Dermoscopy of a skin lesion.
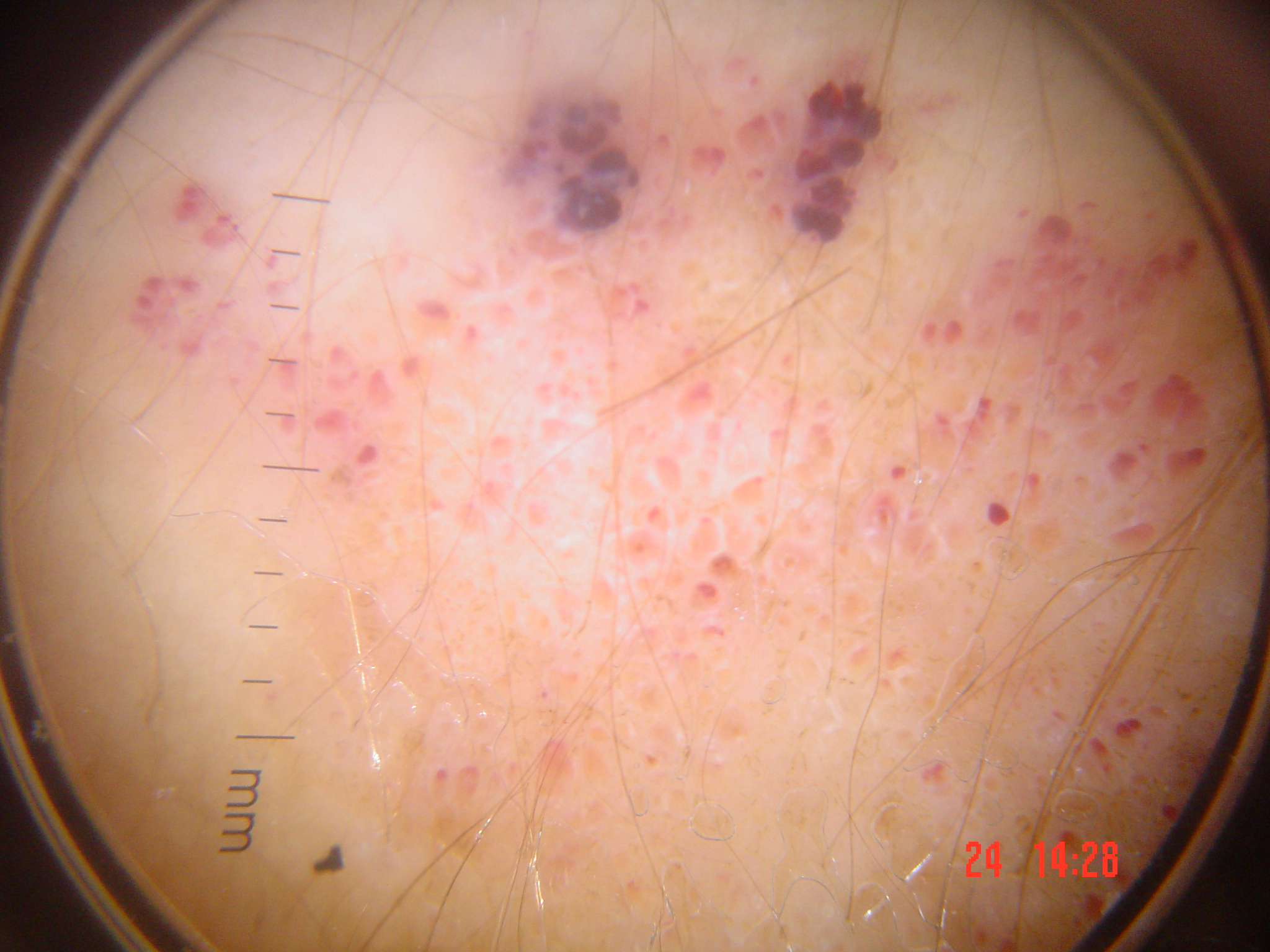Q: What is this lesion?
A: lymphangioma (expert consensus)